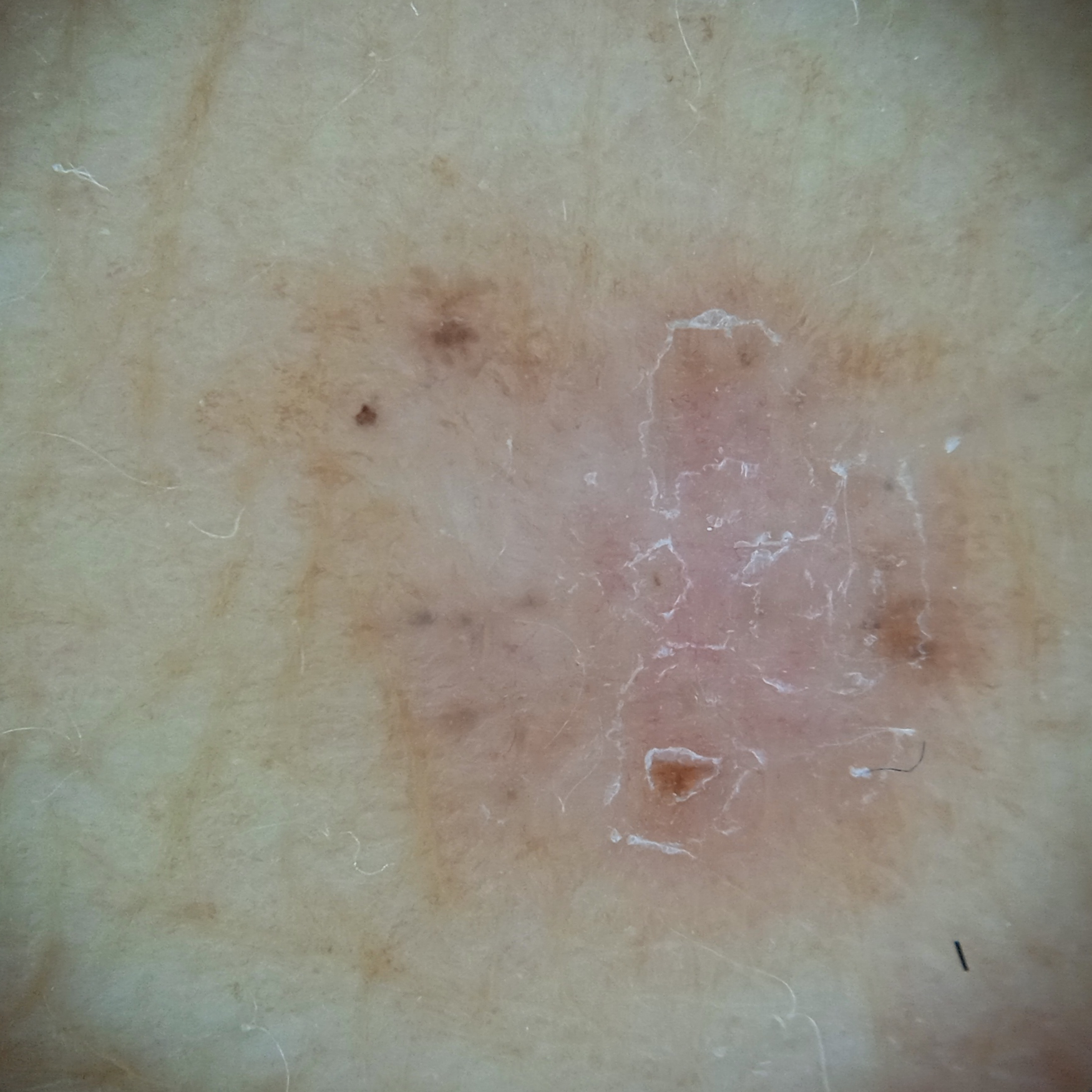sun_reaction: skin tans without first burning
risk_factors:
  positive:
    - a personal history of cancer
    - a family history of skin cancer
mole_burden: a moderate number of melanocytic nevi
referral: clinical suspicion of basal cell carcinoma
patient:
  age: 64
  sex: female
diagnosis:
  name: basal cell carcinoma
  malignancy: malignant
  procedure: punch biopsy
  tumor_thickness_mm: 0.6